Imaged for a research study, with no referral diagnosis recorded · dermoscopy of a skin lesion:
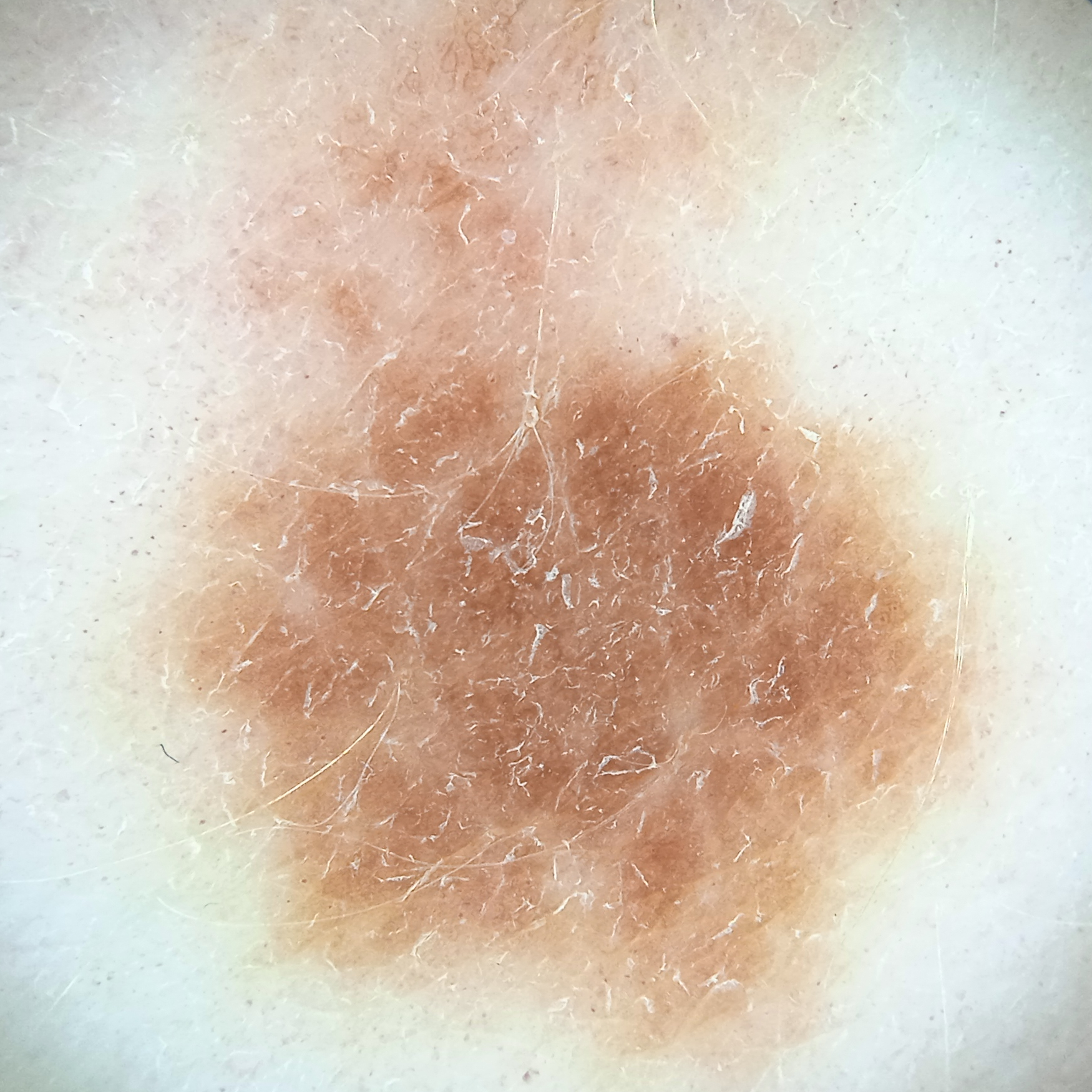Summary: The lesion is located on the torso. The lesion measures approximately 17.5 mm. Assessment: The diagnostic impression was a melanoma.